This is a close-up image. The lesion involves the leg:
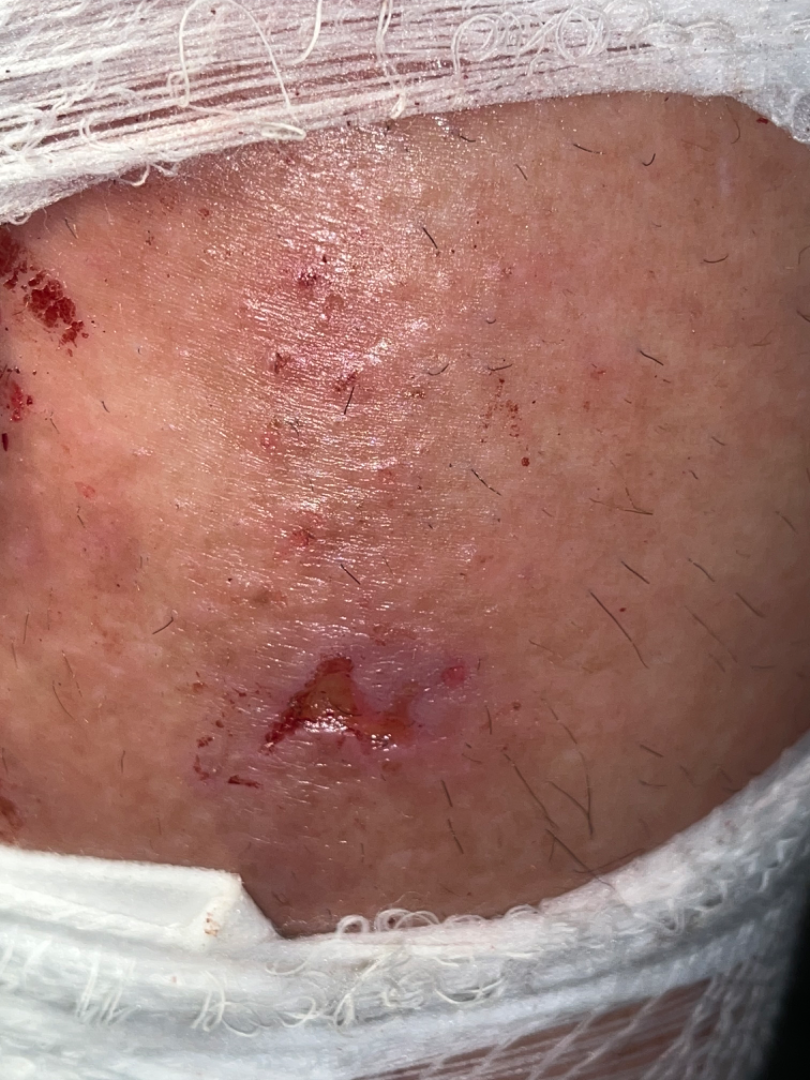<case>
  <differential>
    <leading>Inflicted skin lesions</leading>
    <considered>Herpes Simplex, Pressure ulcer stage 2</considered>
  </differential>
</case>